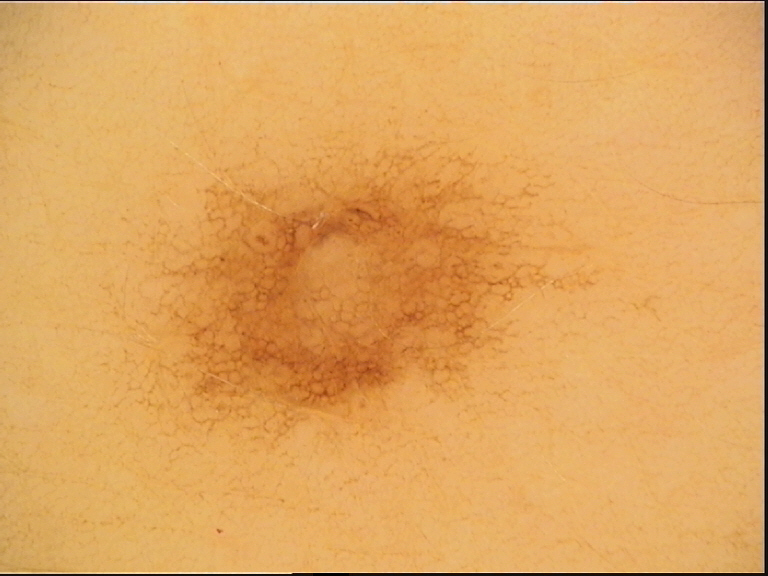A skin lesion imaged with a dermatoscope.
Classified as a benign lesion — a dysplastic junctional nevus.